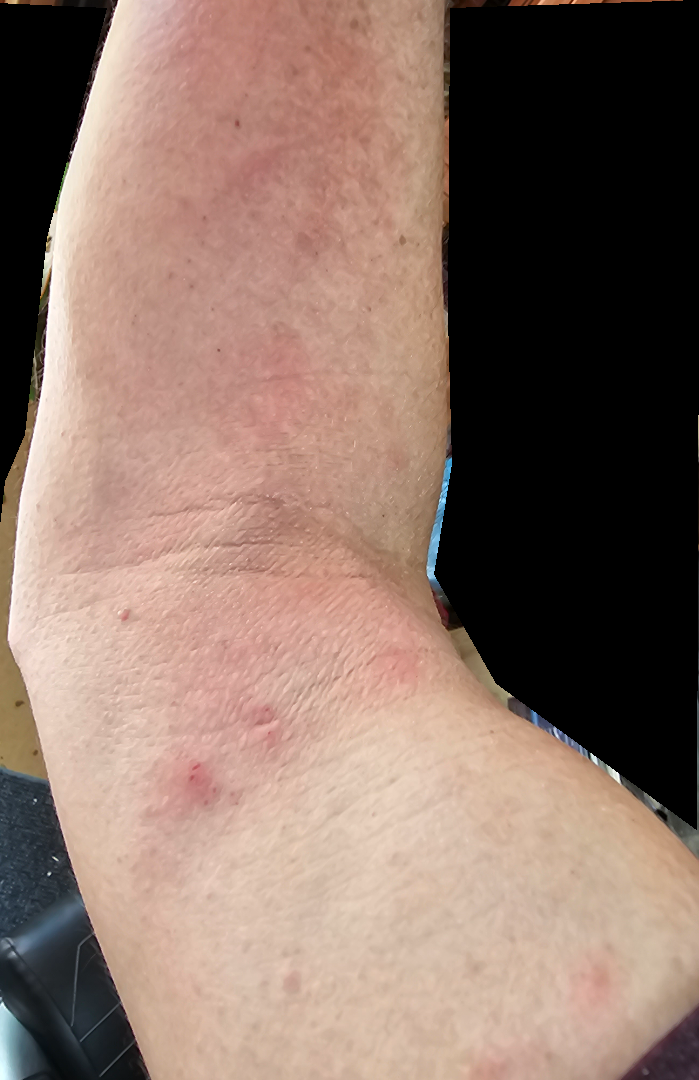Case summary:
• constitutional symptoms — none reported
• anatomic site — front of the torso and arm
• photo taken — at an angle
• history — one to four weeks
• patient-reported symptoms — itching and enlargement
• skin tone — FST III; human graders estimated 2 on the Monk skin tone scale
• texture — raised or bumpy
• assessment — one reviewing dermatologist: the differential includes Photodermatitis, Eczema and Allergic Contact Dermatitis, with no clear leading consideration